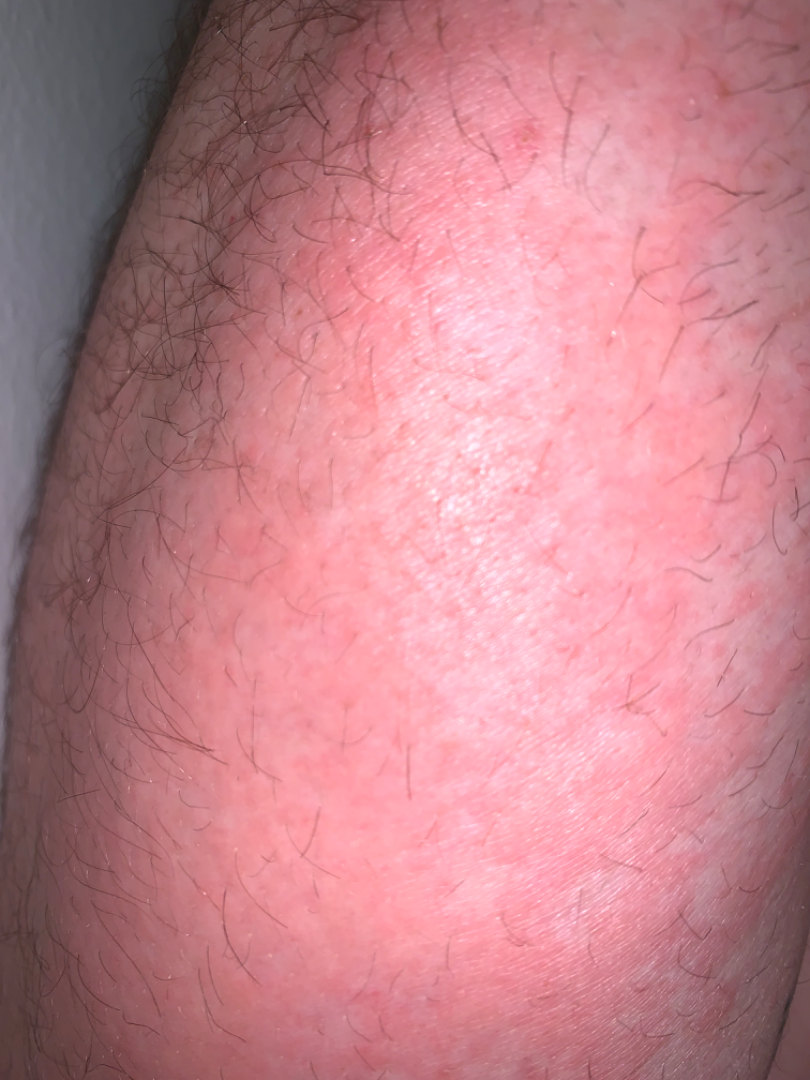Findings:
No differential diagnosis could be assigned on photographic review.
Background:
The lesion is described as raised or bumpy. Reported lesion symptoms include enlargement, itching, pain and burning. The affected area is the leg and arm. Reported duration is less than one week. Close-up view. Associated systemic symptoms include shortness of breath, fatigue and chills.